A subject in their late 60s: 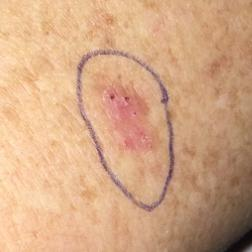The lesion involves an arm. Expert review favored a premalignant lesion — an actinic keratosis.